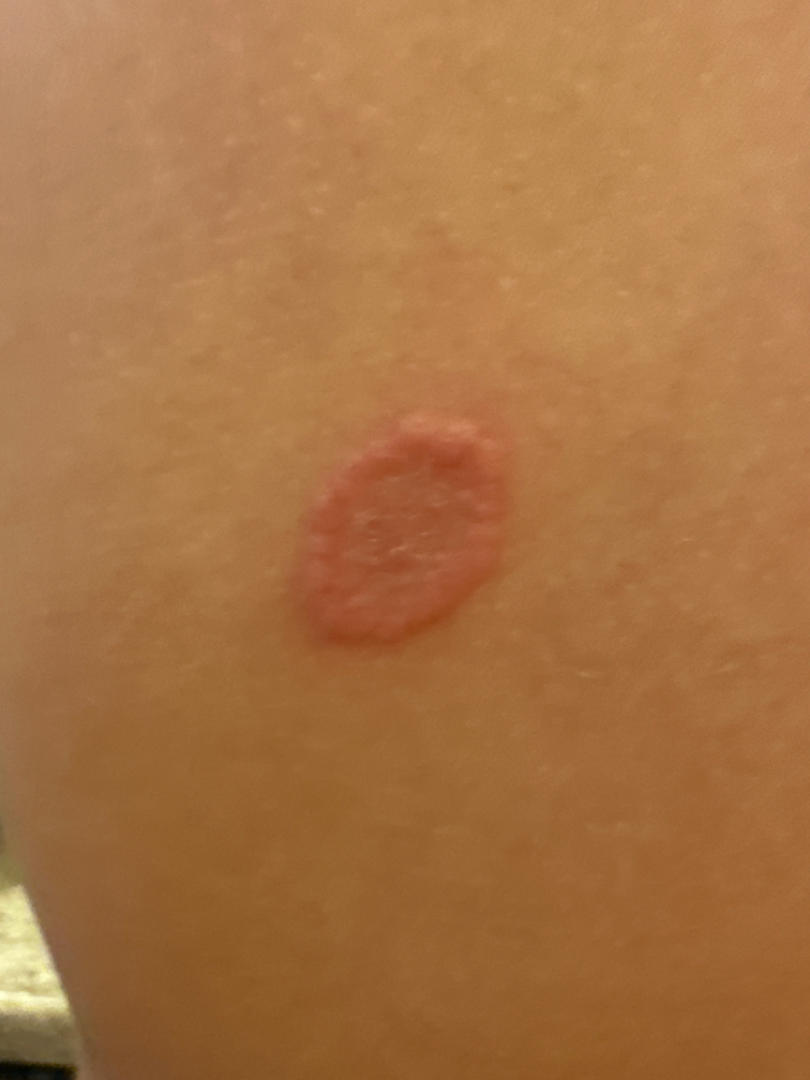assessment=unable to determine
image framing=close-up
systemic symptoms=none reported
skin tone=self-reported Fitzpatrick IV; non-clinician graders estimated MST 3 or 4
lesion symptoms=itching and bothersome appearance
subject=male, age 18–29
patient's own categorization=skin that appeared healthy to them
site=back of the torso
lesion texture=raised or bumpy
symptom duration=less than one week